A male subject roughly 70 years of age; a clinical photograph showing a skin lesion in context.
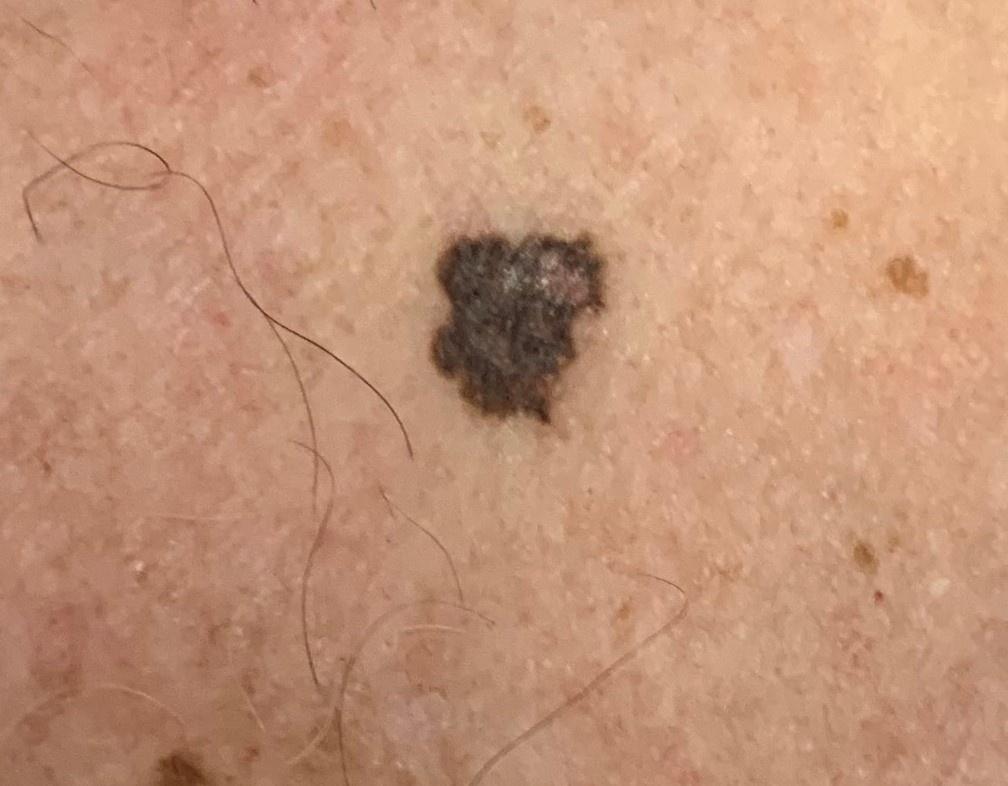location=the trunk (the anterior trunk) | diagnosis=Melanoma (biopsy-proven).